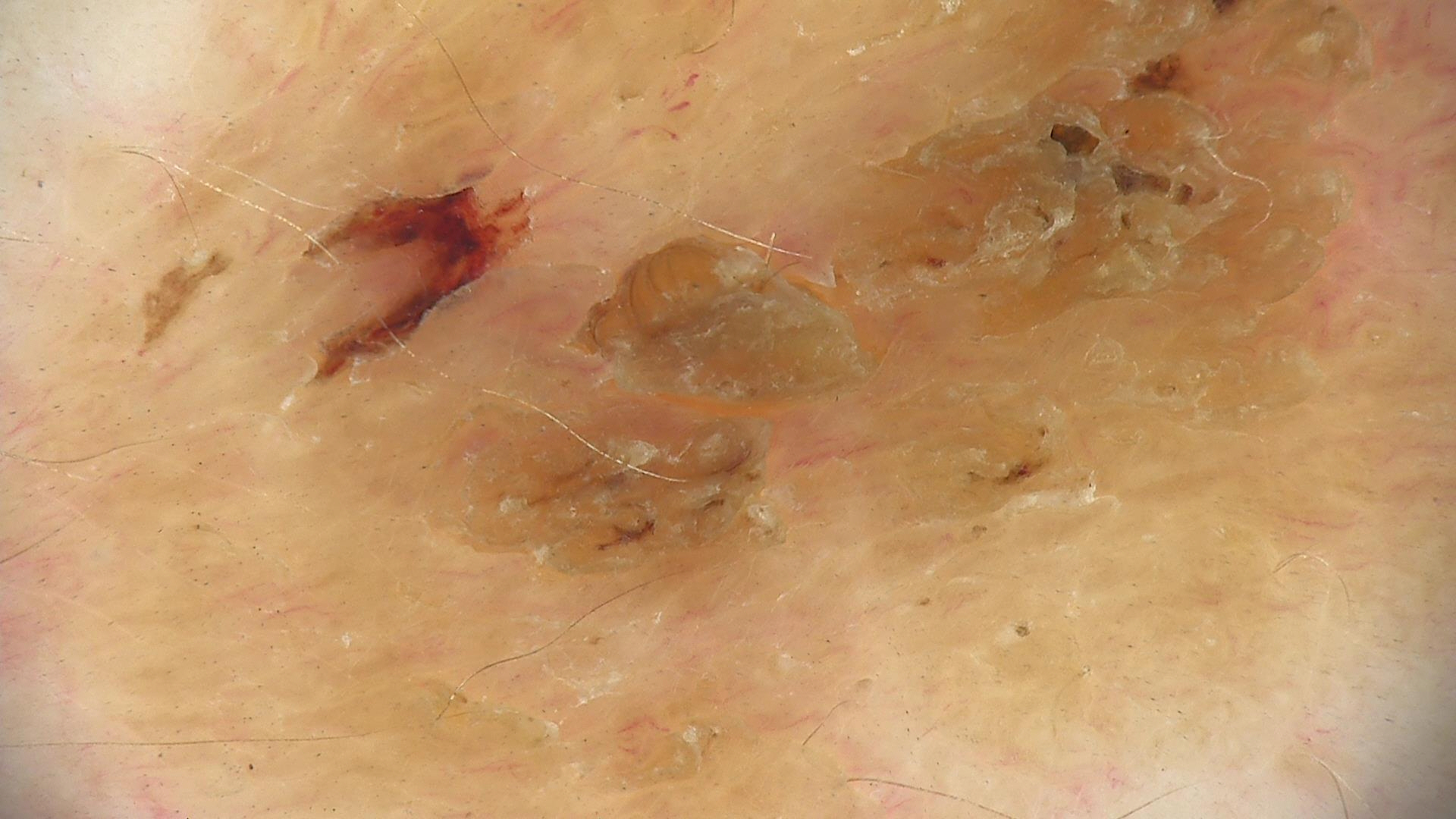class: seborrheic keratosis (expert consensus).